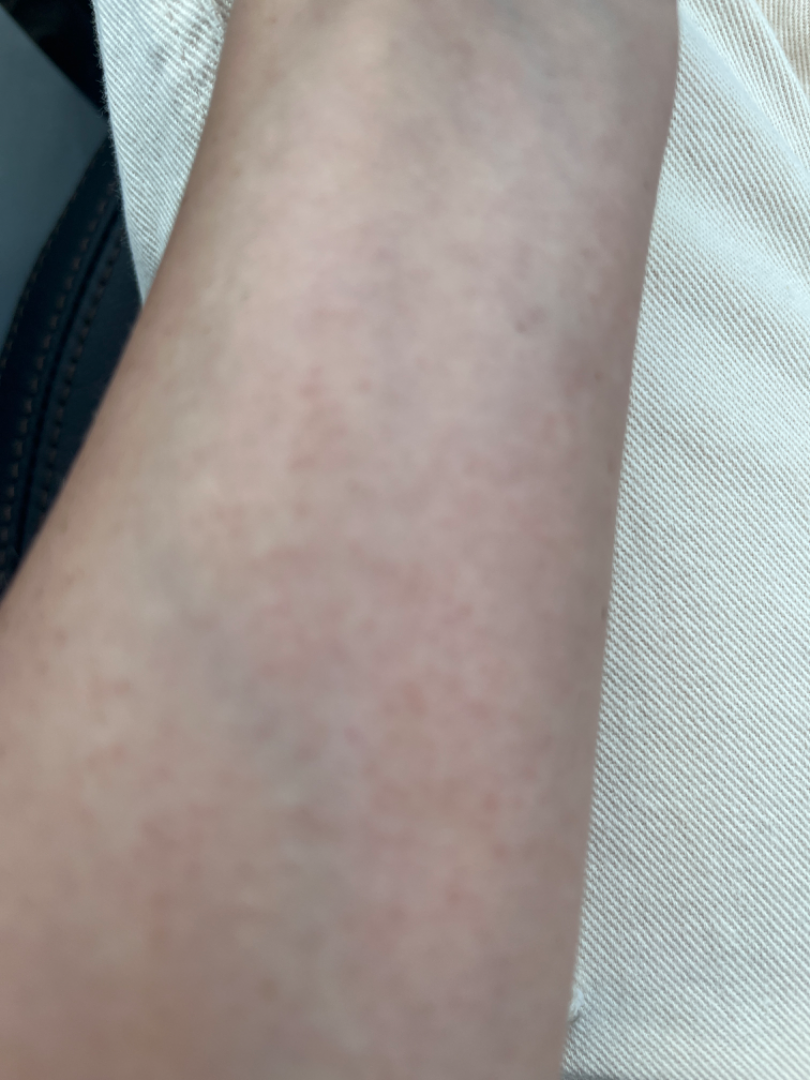assessment = not assessable, image framing = close-up, patient = female.